The photograph is a close-up of the affected area; located on the arm: 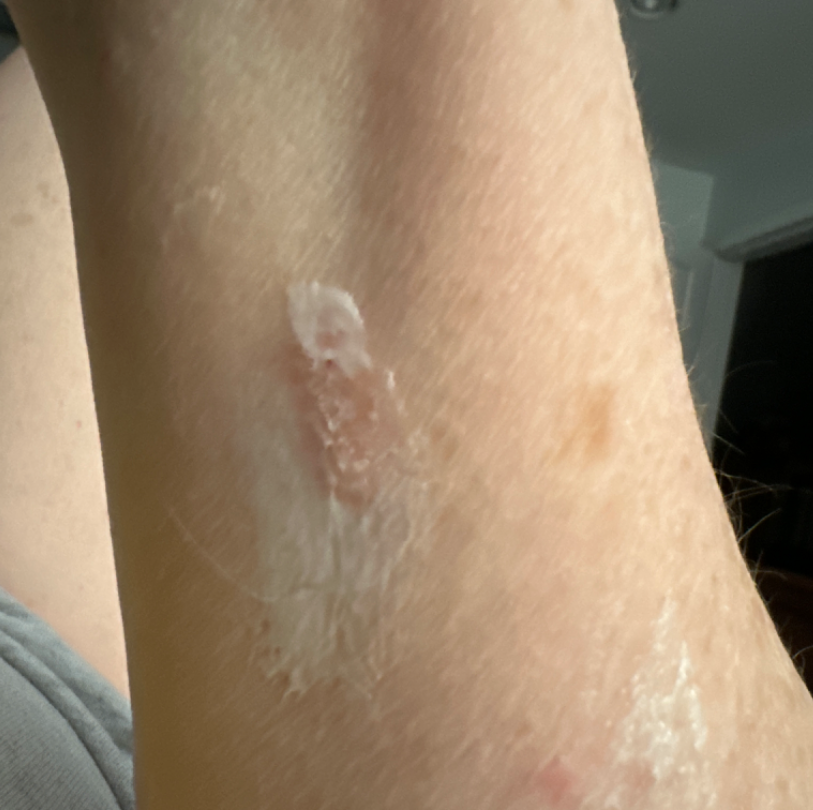The skin condition could not be confidently assessed from this image. Skin tone: Fitzpatrick II. Reported duration is one to four weeks. Texture is reported as raised or bumpy. The patient described the issue as a rash.